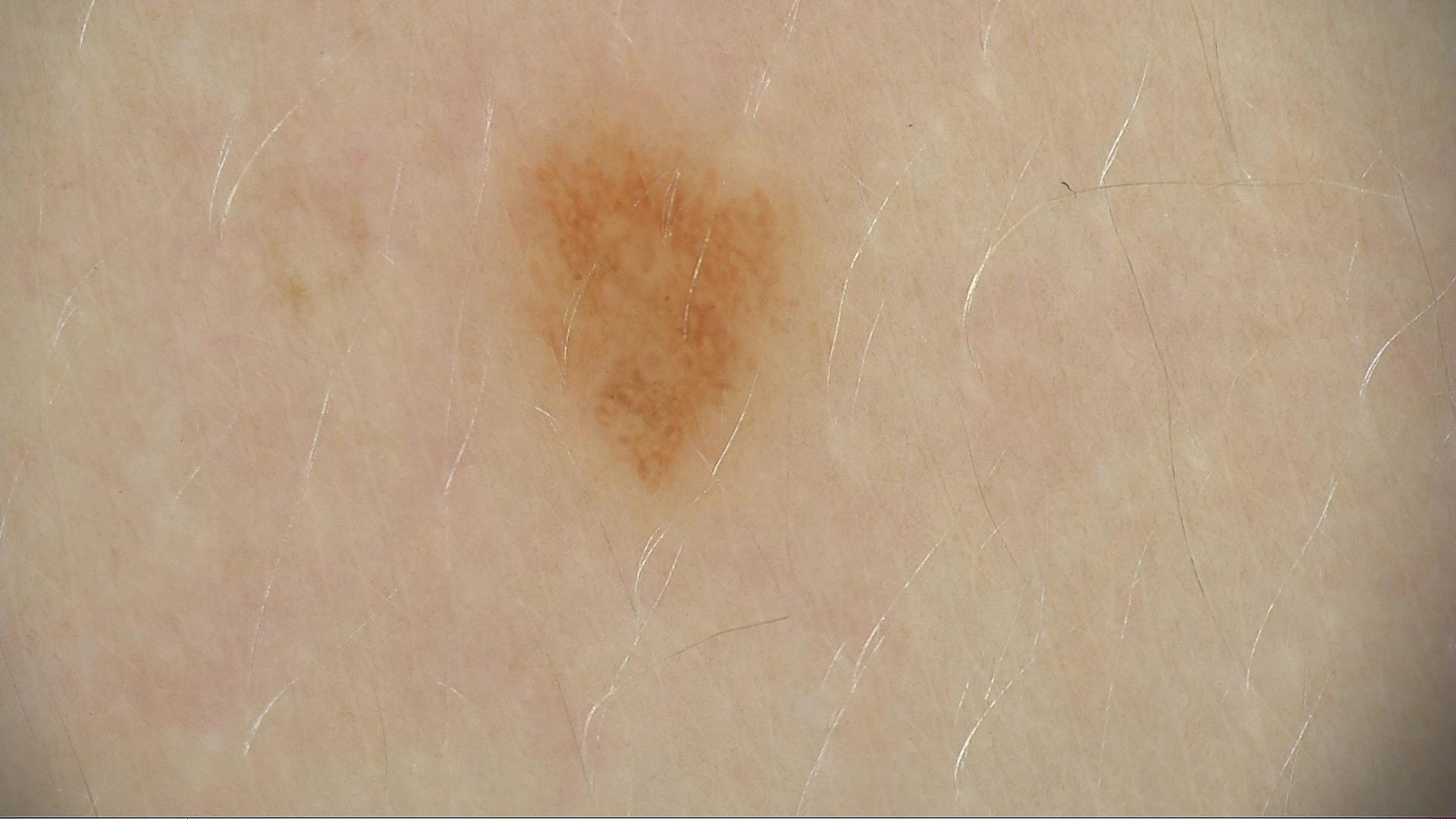A dermoscopy image of a single skin lesion.
Classified as a dysplastic junctional nevus.